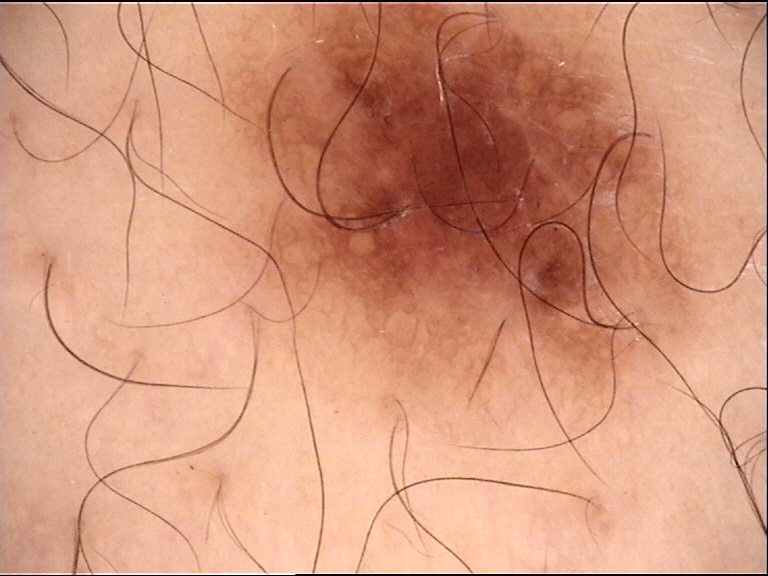diagnosis — dysplastic junctional nevus (expert consensus).